Dermoscopy of a skin lesion: 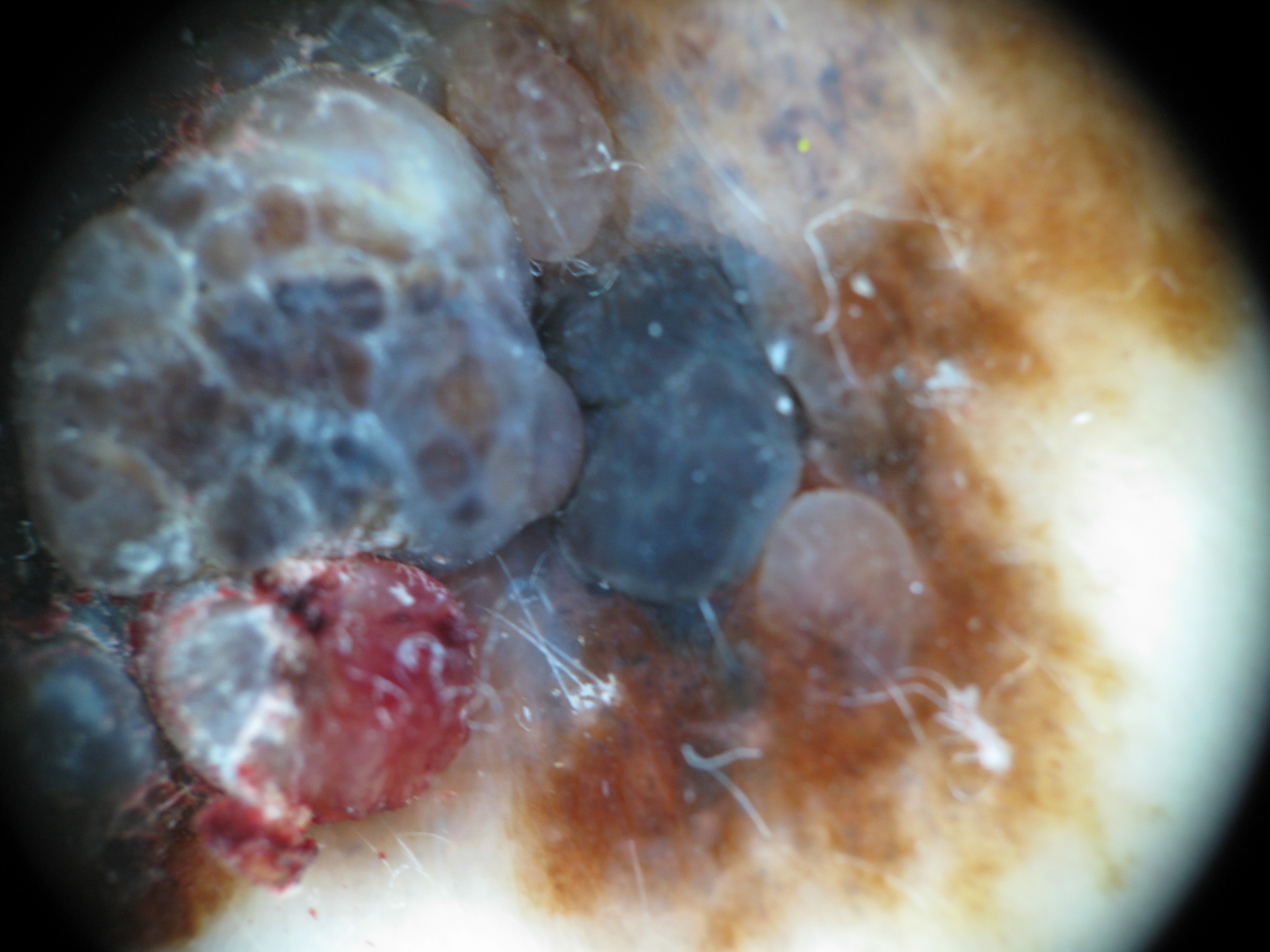Q: What is the diagnosis?
A: melanoma (biopsy-proven)